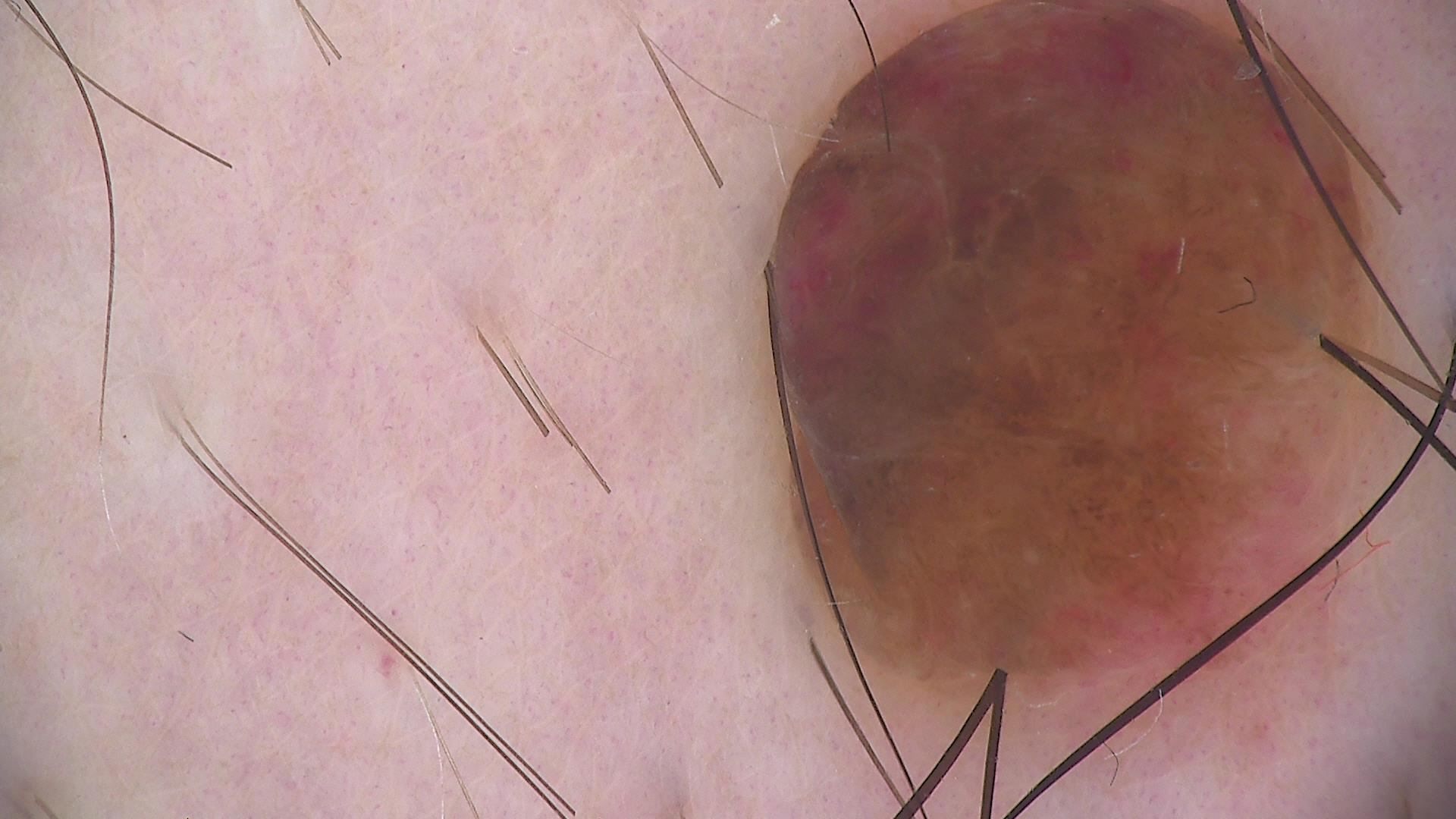| key | value |
|---|---|
| imaging | dermoscopy |
| diagnostic label | dermal nevus (expert consensus) |